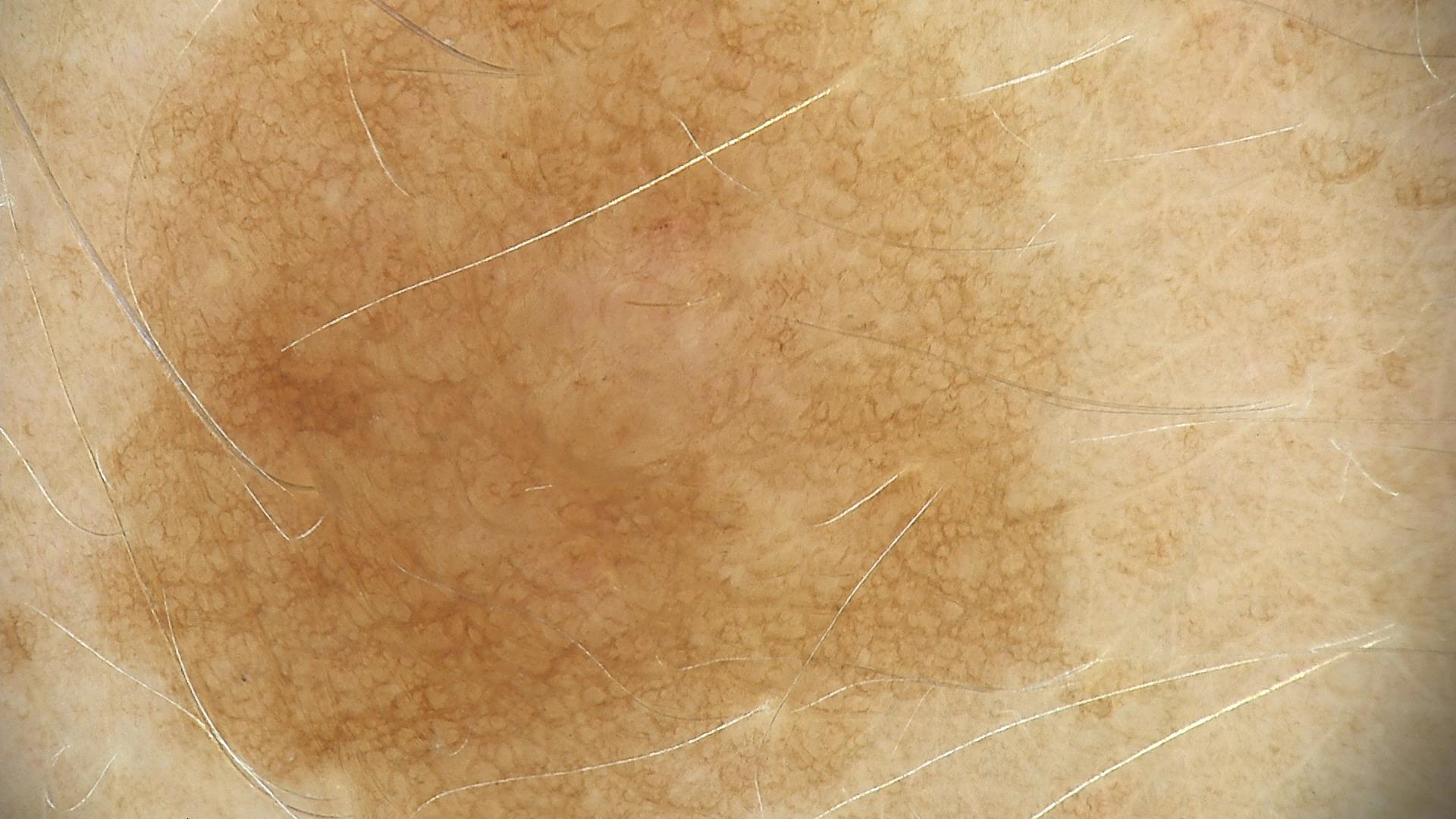Impression:
Diagnosed as a solar lentigo.